This is a dermoscopic photograph of a skin lesion — 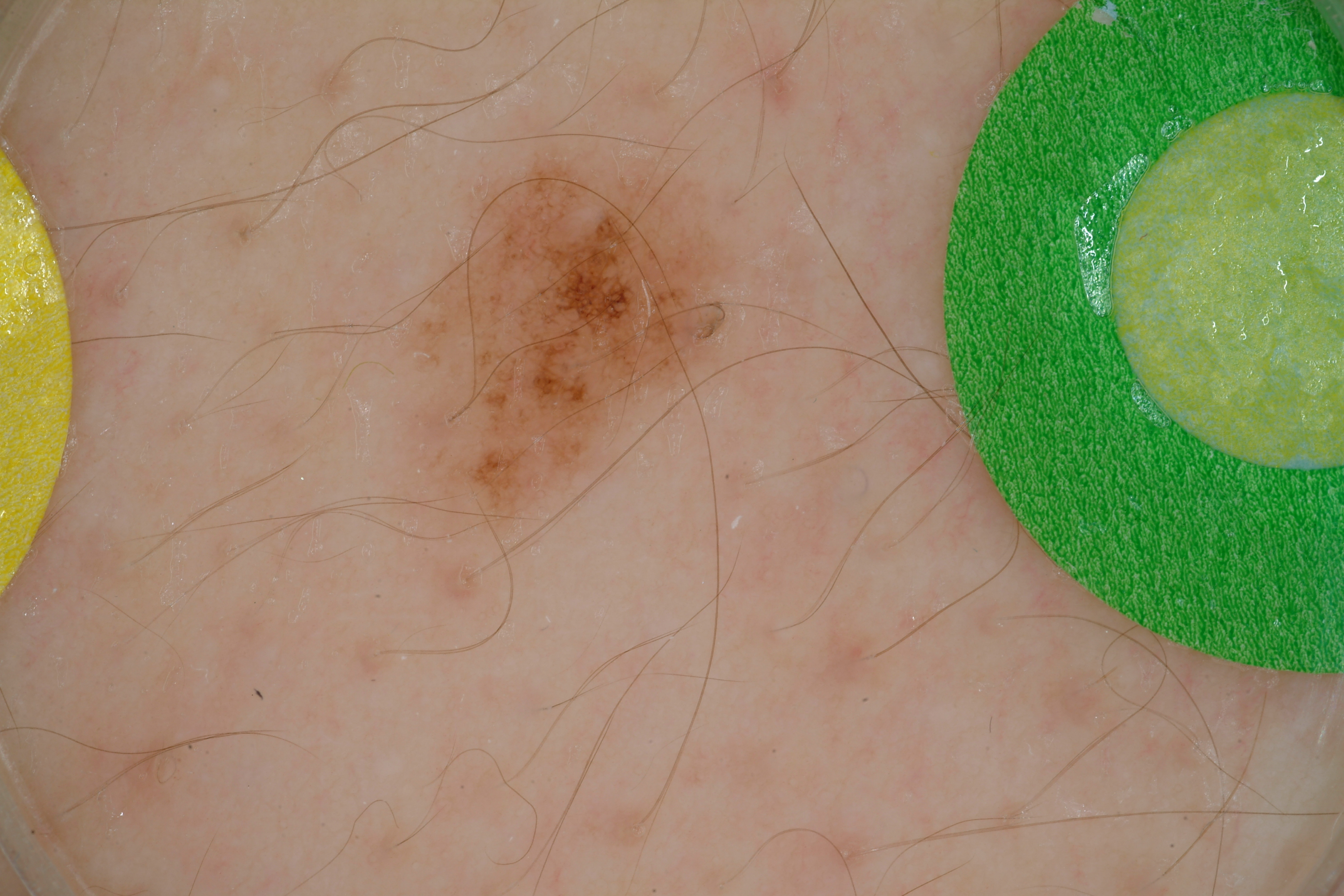Summary: Dermoscopic examination shows globules. With coordinates (x1, y1, x2, y2), the lesion spans 383, 134, 787, 547. Conclusion: The lesion was assessed as a benign lesion.